Close-up view · the condition has been present for less than one week · located on the leg · the lesion is associated with bothersome appearance, burning and itching: 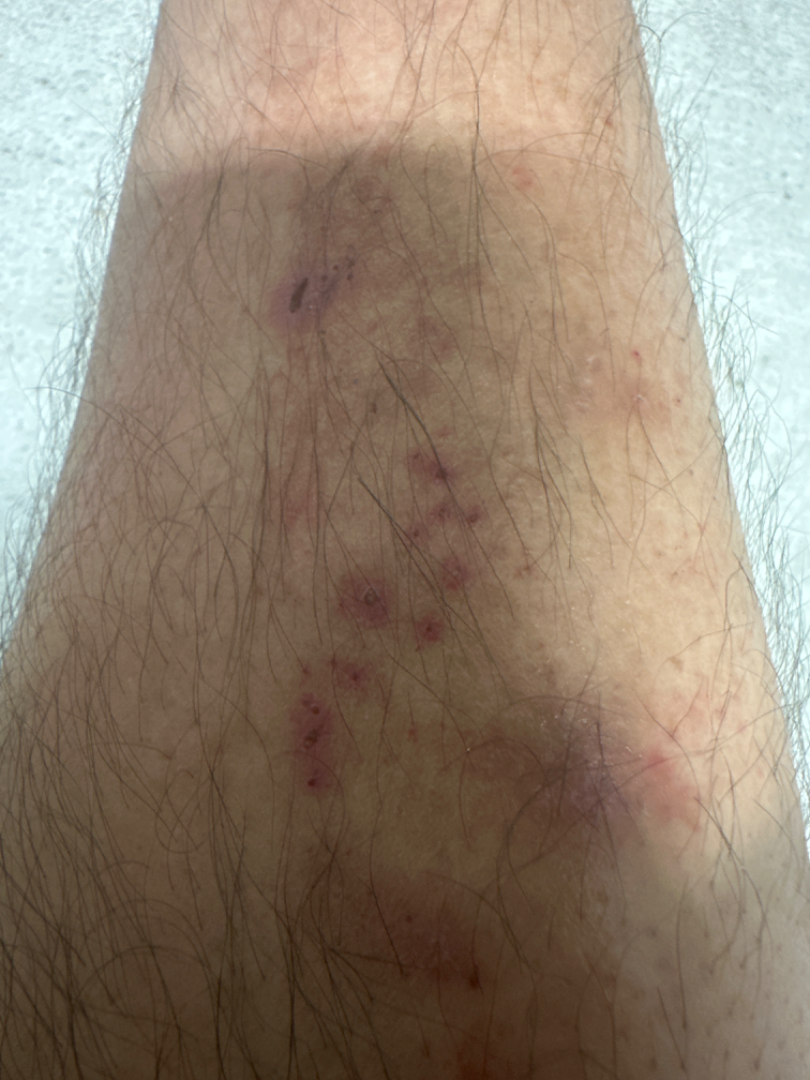- assessment — ungradable on photographic review